A skin lesion imaged with a dermatoscope.
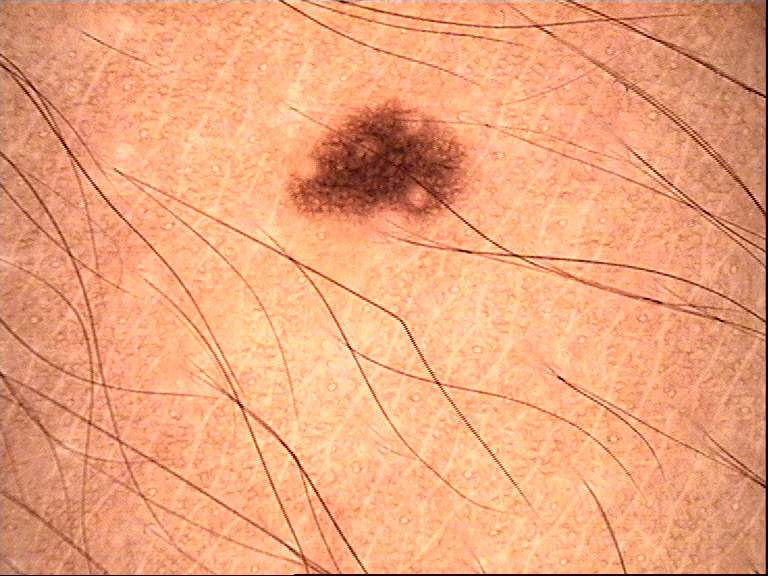The diagnostic label was a benign lesion — a dysplastic junctional nevus.